The photograph was taken at an angle · located on the head or neck, sole of the foot, arm, front of the torso, top or side of the foot, back of the torso and leg:
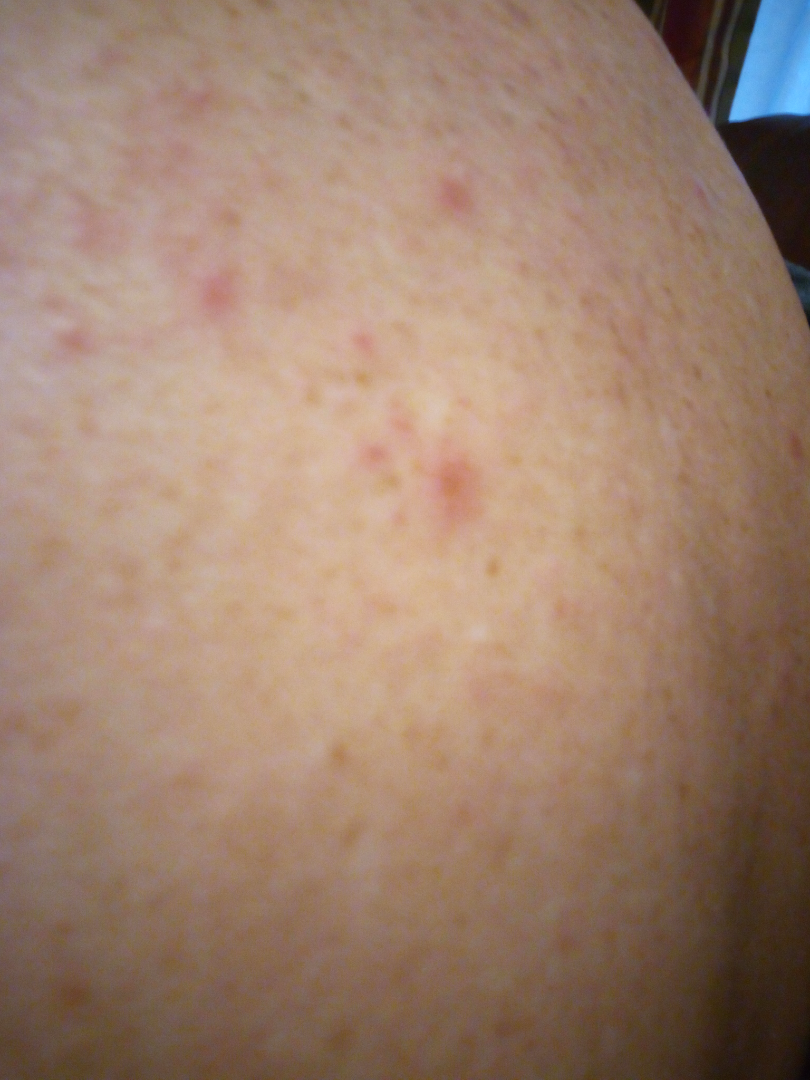Review:
The skin findings could not be characterized from the image.